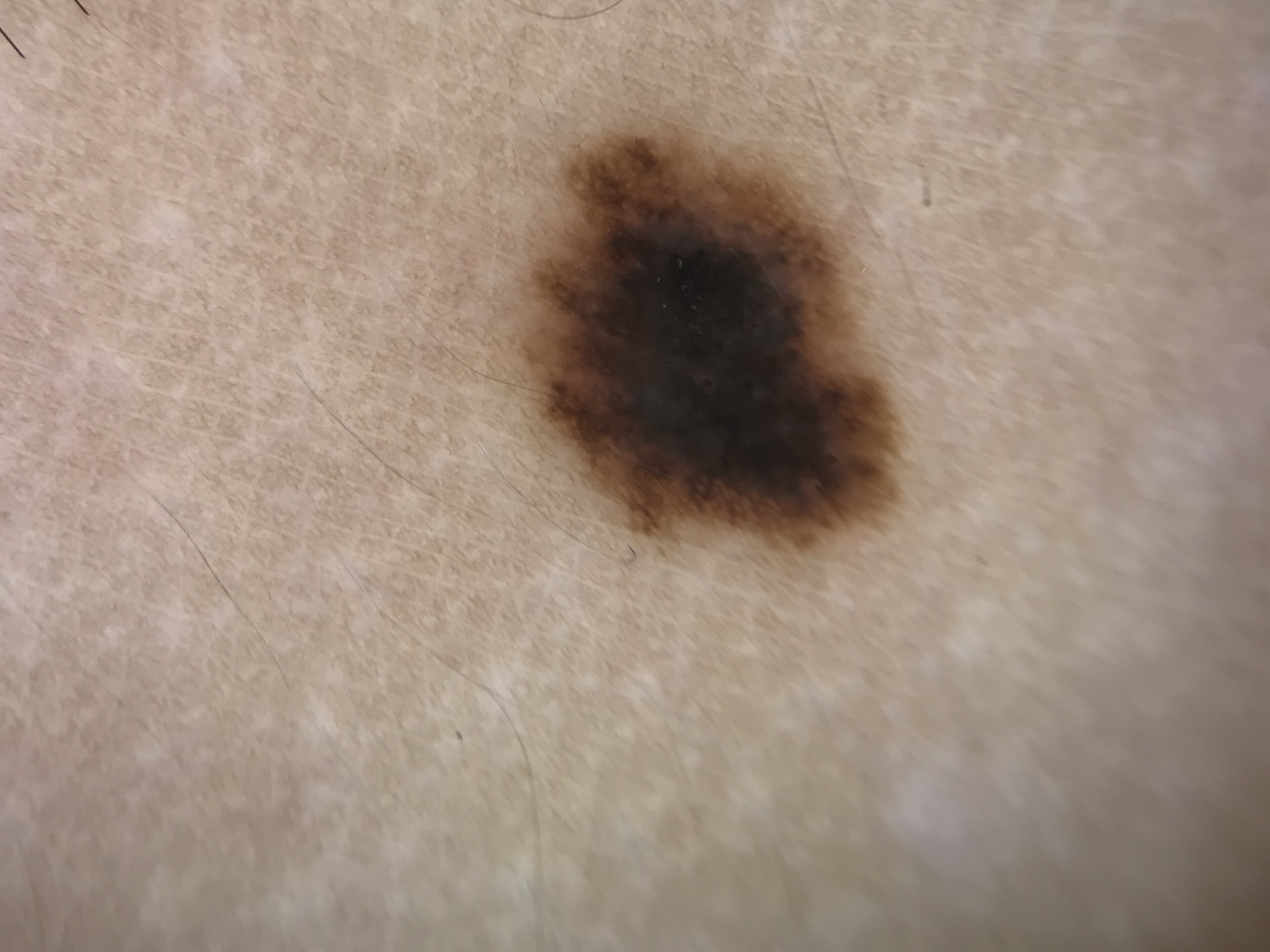A dermoscopic image of a skin lesion.
Classified as a benign lesion — a dysplastic junctional nevus.